A skin lesion imaged with contact-polarized dermoscopy; a female subject approximately 20 years of age — 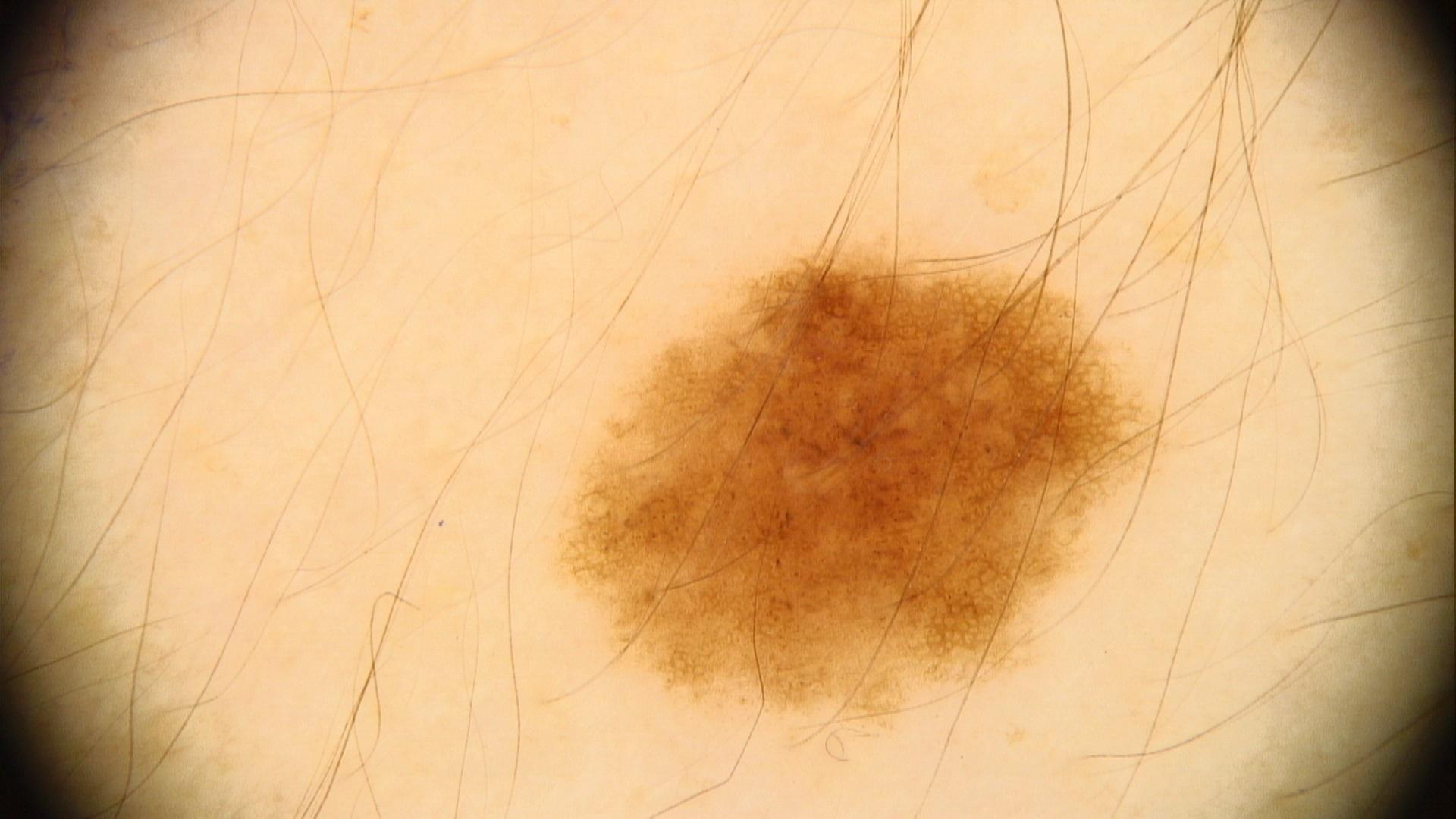The lesion is on an upper extremity. The diagnostic impression was a nevus.